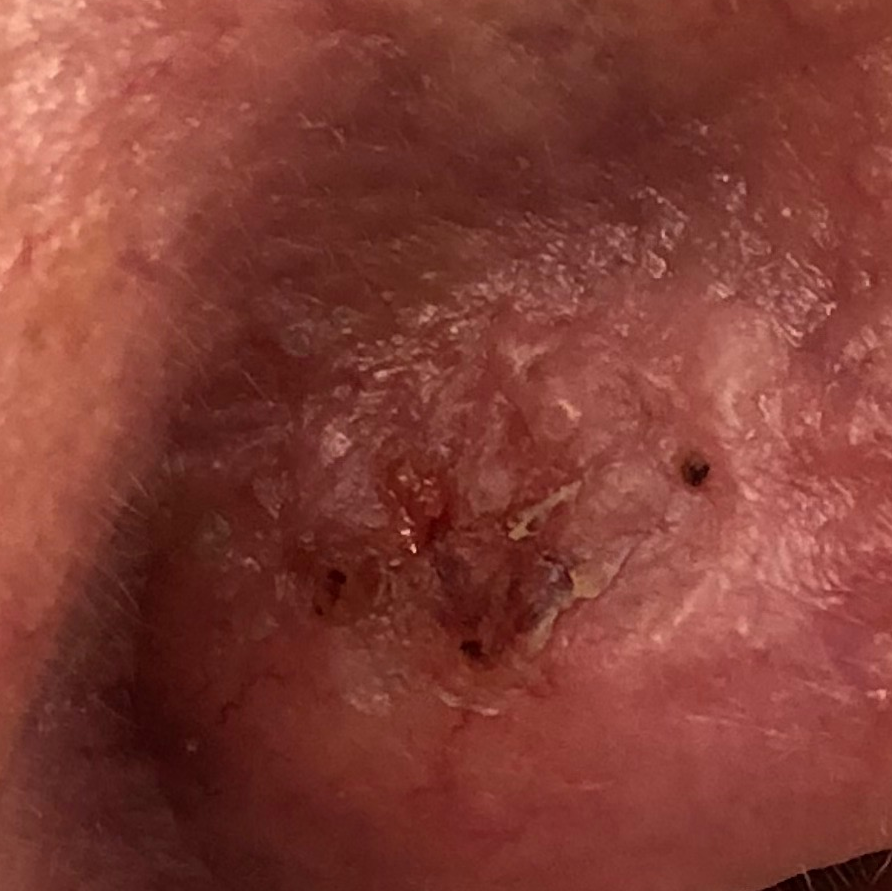Q: What is this lesion?
A: basal cell carcinoma (biopsy-proven)